The lesion involves the leg, a close-up photograph.
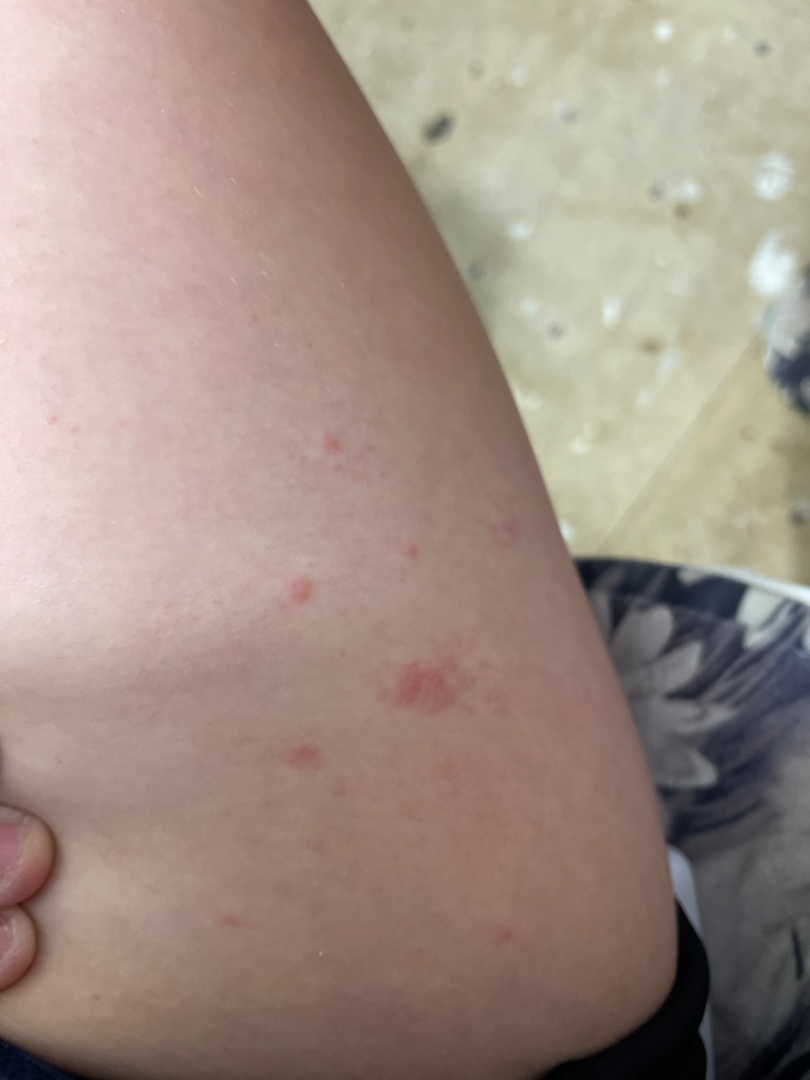Background:
Reported duration is less than one week. Symptoms reported: bothersome appearance. Texture is reported as raised or bumpy.
Findings:
Favoring Eczema; an alternative is Urticaria.